History notes prior skin cancer (patient or family), alcohol use, pesticide exposure, and prior malignancy (patient or family); a male subject 62 years of age; a clinical photograph showing a skin lesion.
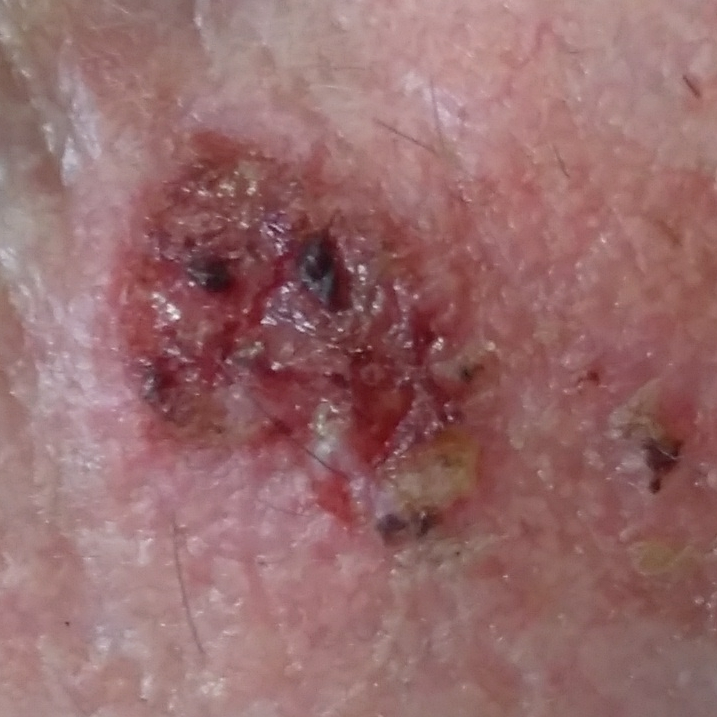Q: Where on the body is the lesion?
A: the face
Q: What are the lesion's dimensions?
A: 14x12 mm
Q: What did the workup show?
A: basal cell carcinoma (biopsy-proven)